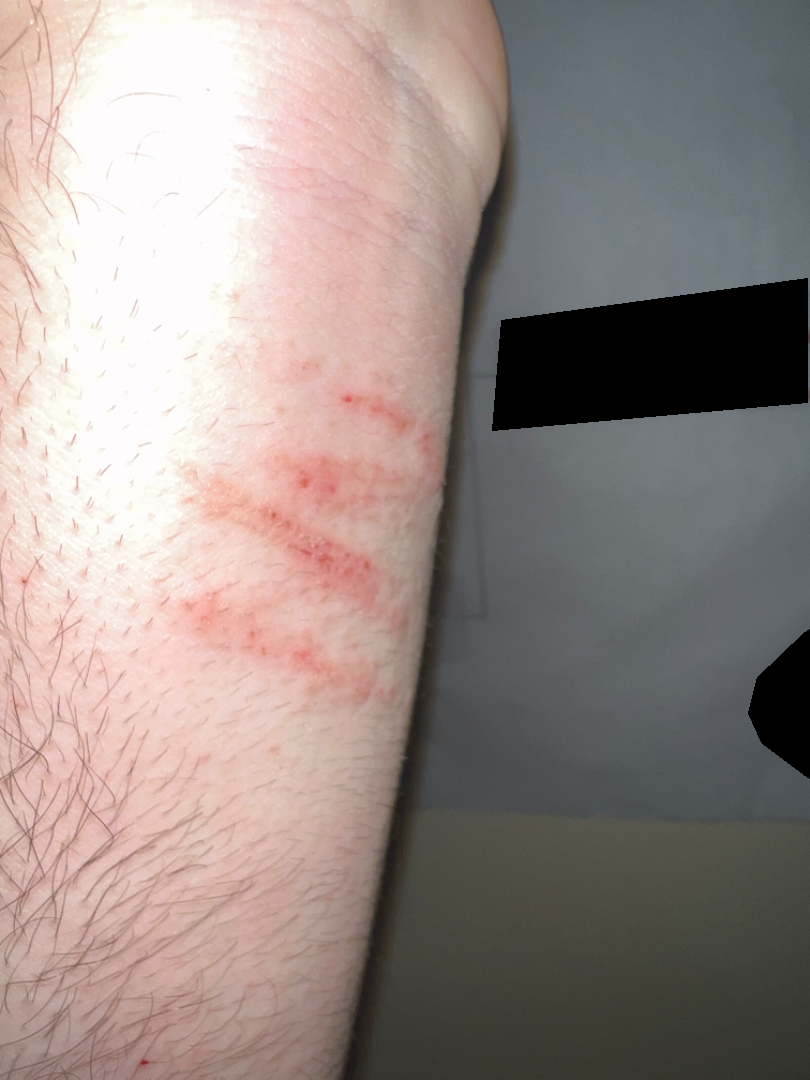The patient reported no systemic symptoms. The photo was captured at an angle. Self-categorized by the patient as a rash. The contributor notes the condition has been present for one to four weeks. Fitzpatrick phototype II; lay reviewers estimated Monk Skin Tone 1 or 2 (two reviewer pools). The affected area is the arm. Reported lesion symptoms include itching and enlargement. The subject is 18–29, male. The contributor notes the lesion is raised or bumpy. On dermatologist assessment of the image: most consistent with Allergic Contact Dermatitis.